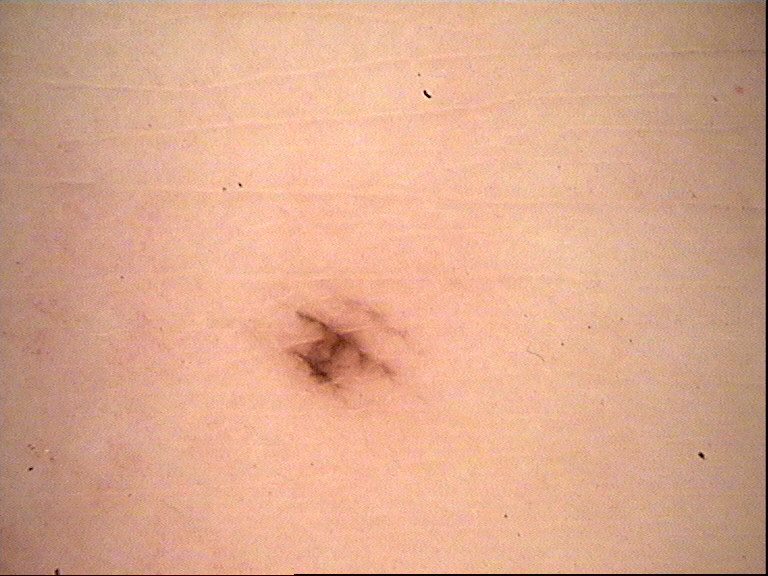Conclusion:
Diagnosed as an acral dysplastic junctional nevus.